A dermoscopic photograph of a skin lesion.
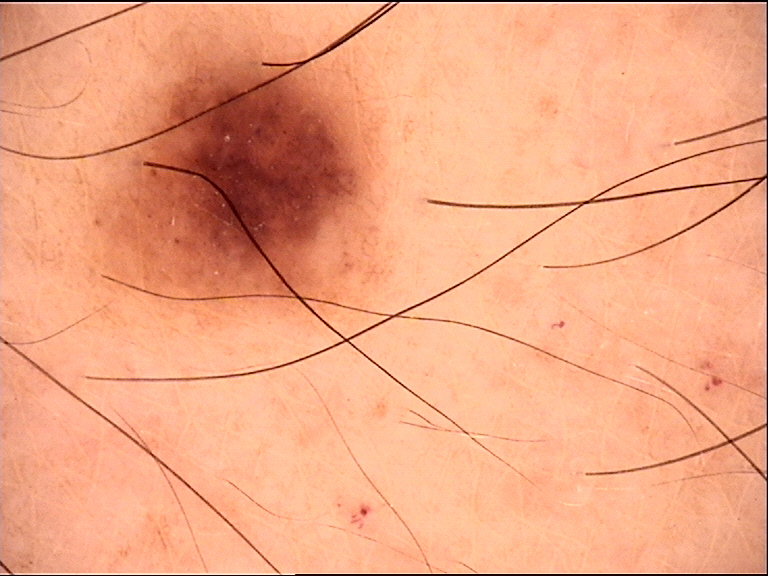Q: What was the diagnostic impression?
A: dysplastic junctional nevus (expert consensus)